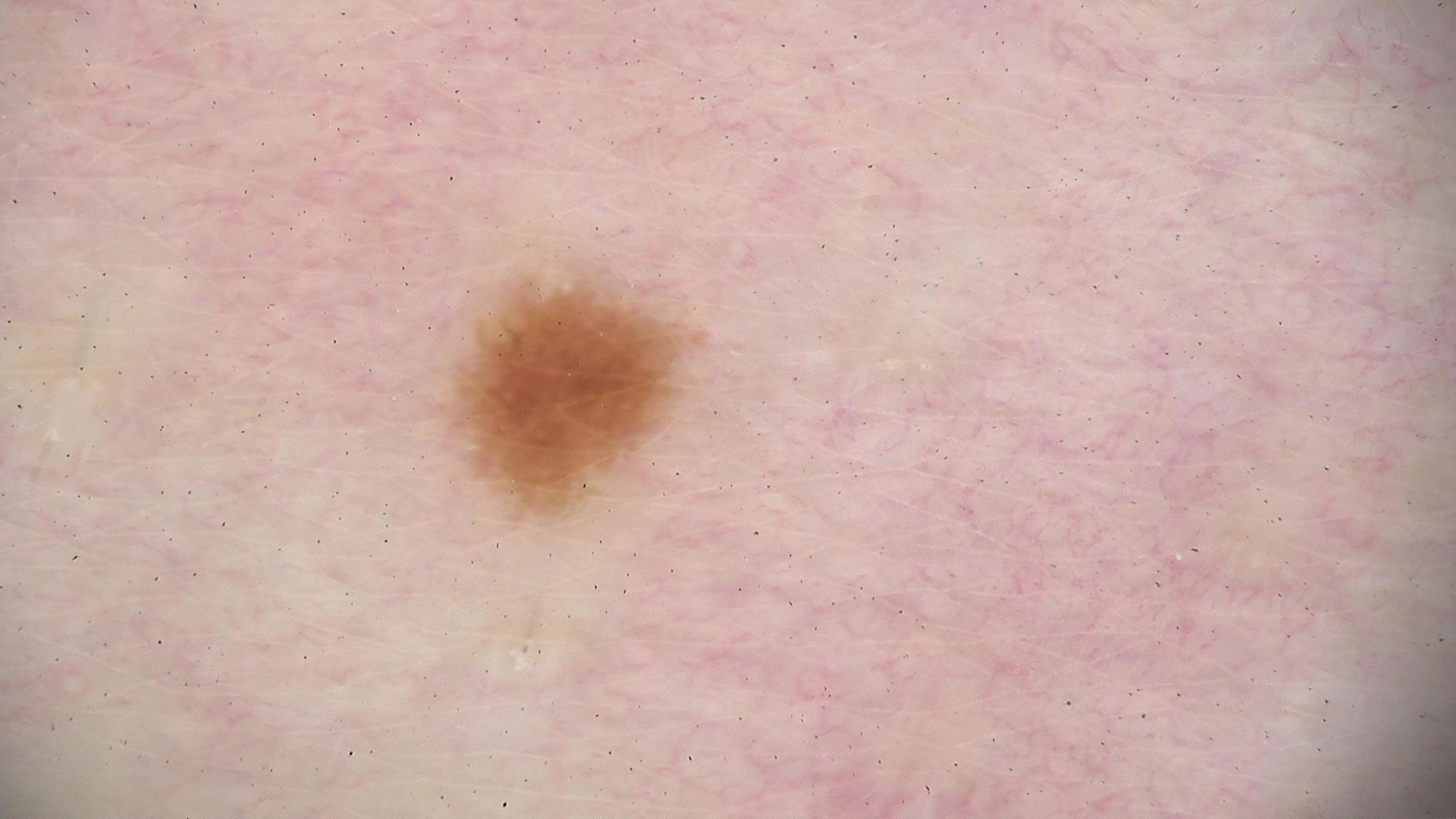Case:
- diagnostic label: junctional nevus (expert consensus)